A dermatoscopic image of a skin lesion.
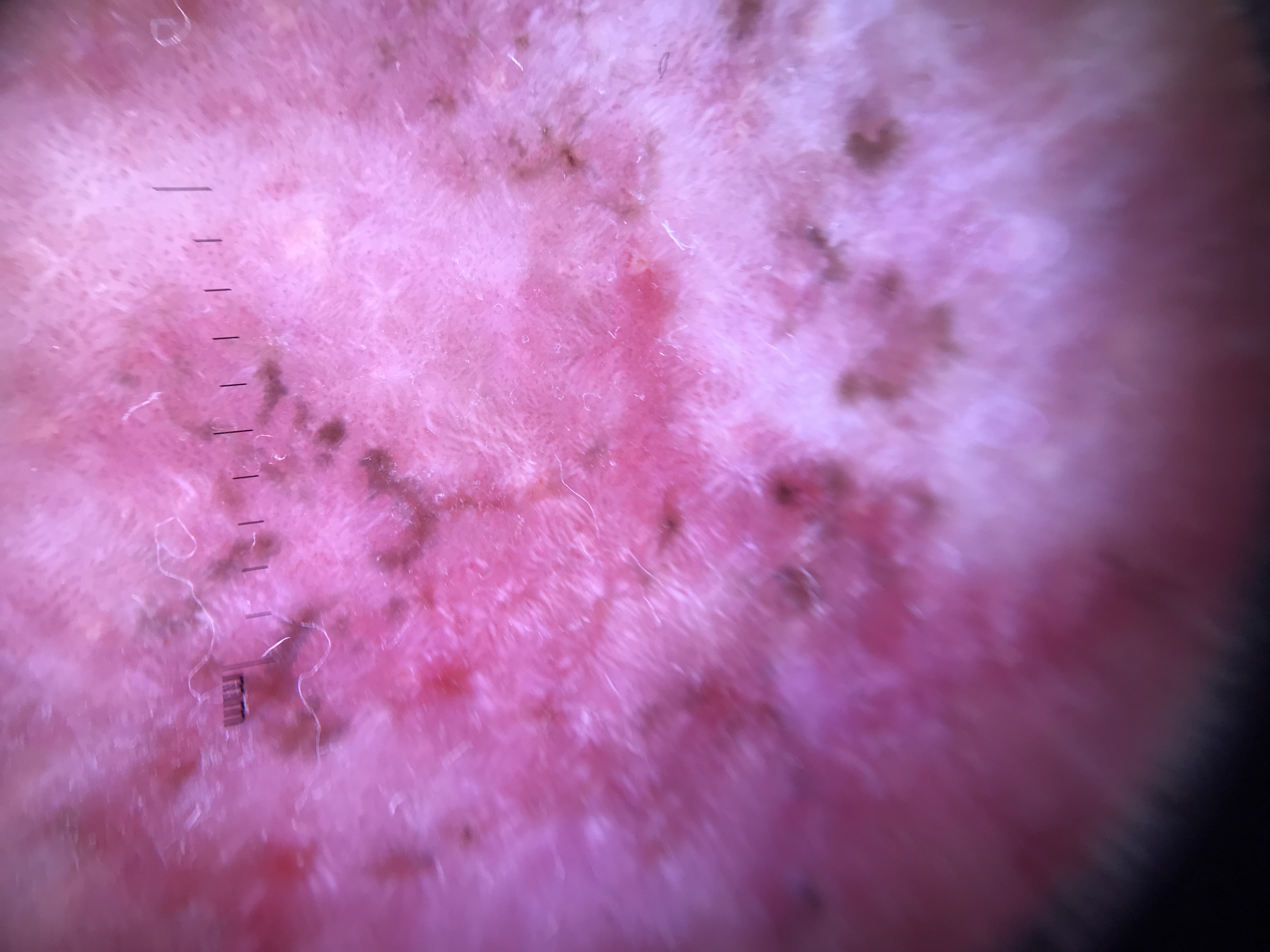class = basal cell carcinoma (biopsy-proven)